A dermoscopic close-up of a skin lesion:
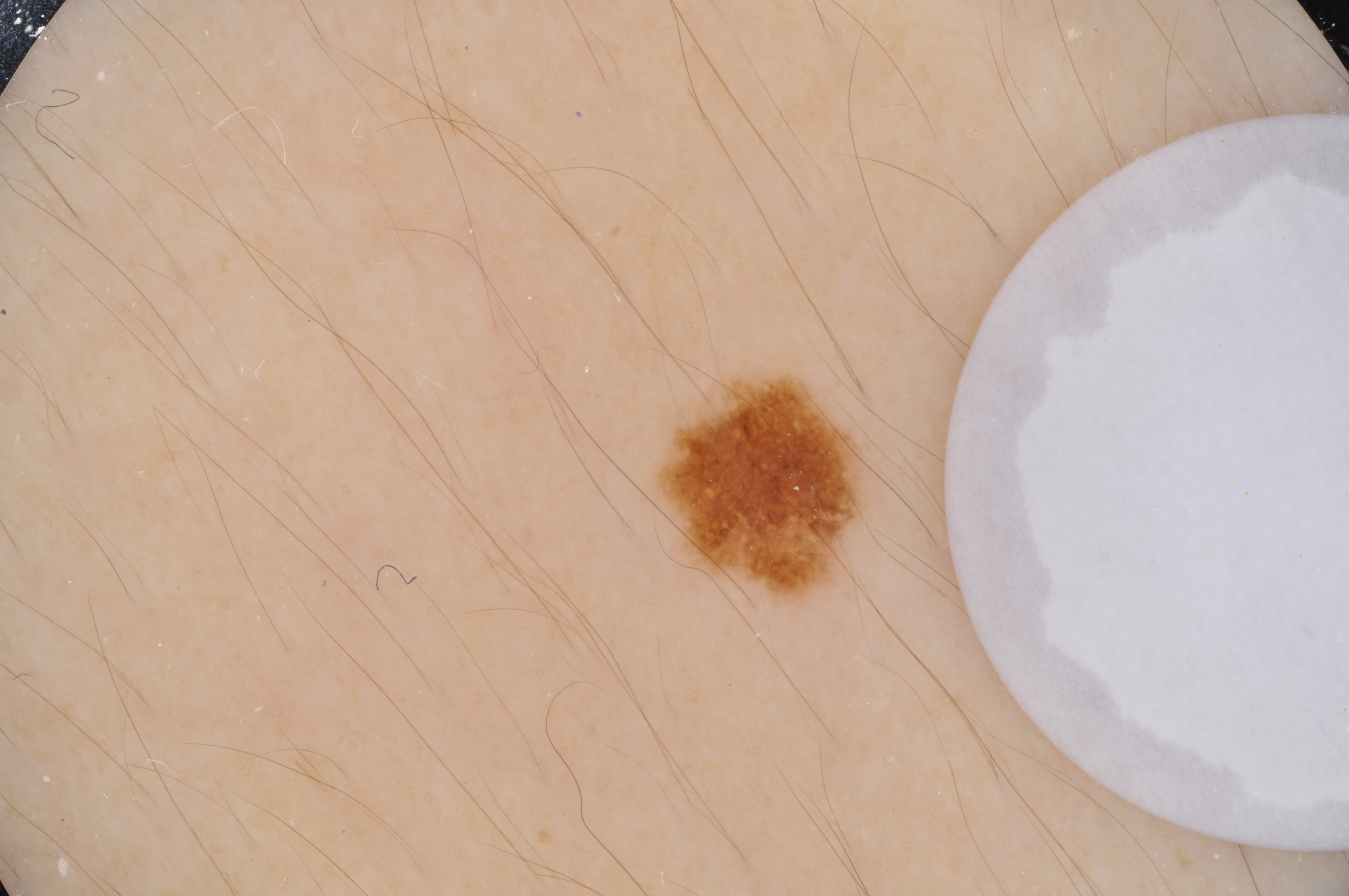Case summary:
The lesion is bounded by x1=651 y1=366 x2=871 y2=606.
Impression:
Consistent with a melanocytic nevus, a benign skin lesion.